The photograph is a close-up of the affected area · the affected area is the back of the hand: 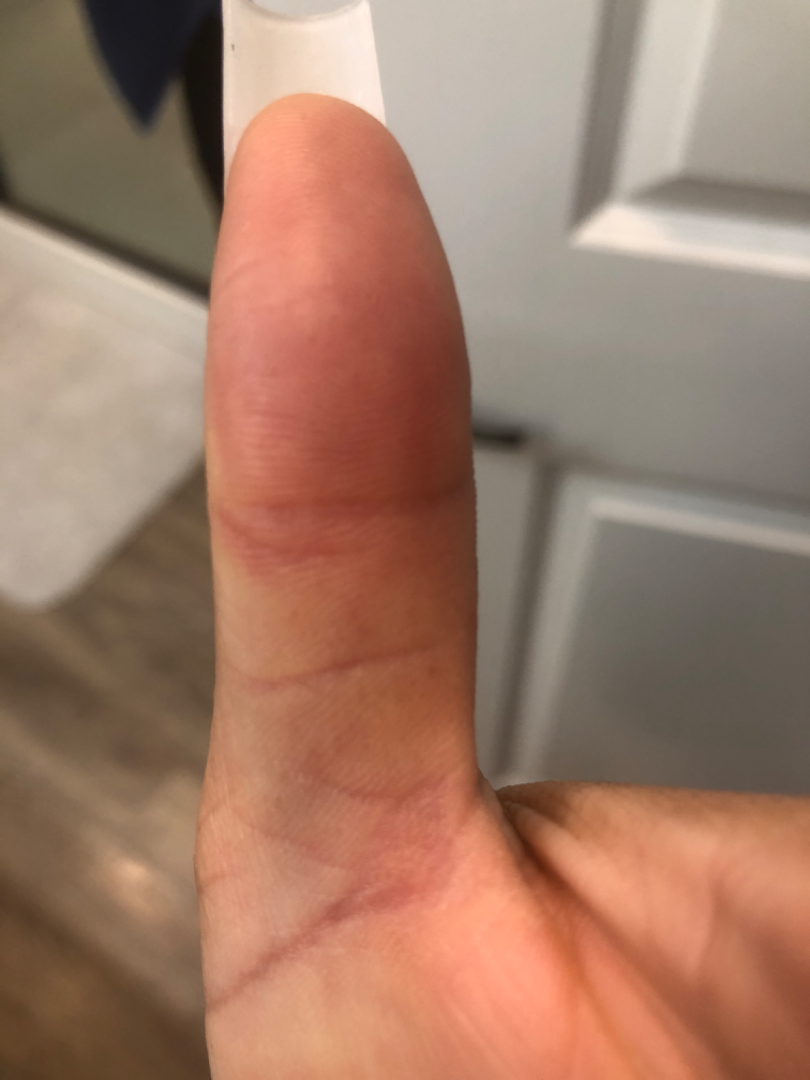The image was not sufficient for the reviewer to characterize the skin condition.